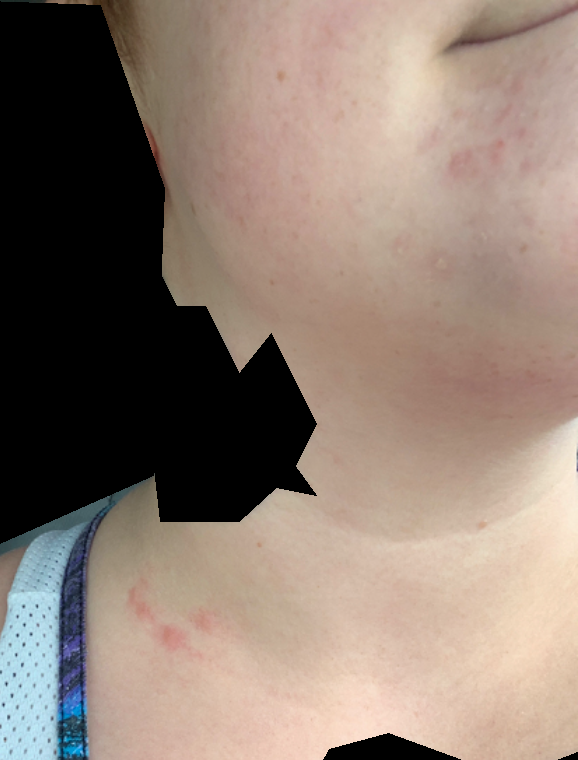Review:
The skin findings could not be characterized from the image.
Patient information:
The condition has been present for about one day. The affected area is the head or neck. The patient considered this a rash. This image was taken at a distance.